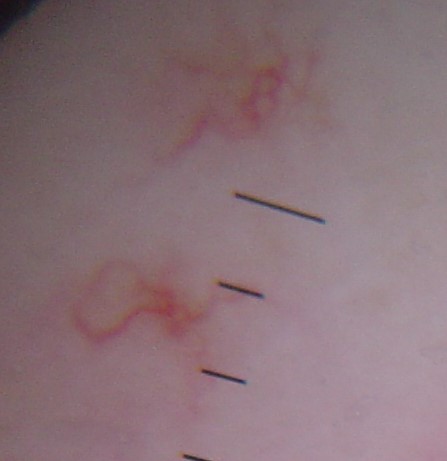A dermoscopic photograph of a skin lesion.
Consistent with a vascular lesion — a spider angioma.